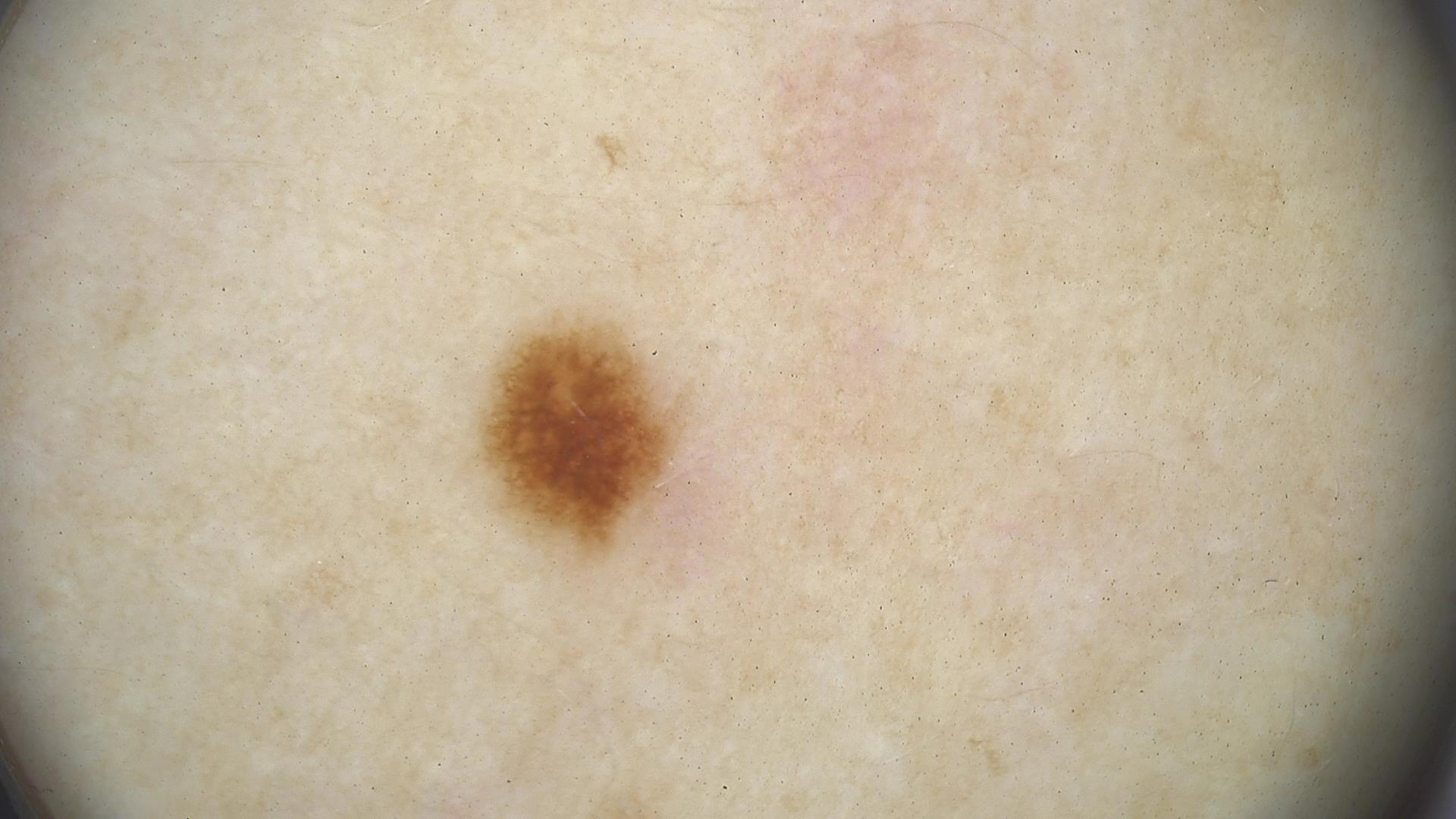A dermoscopic image of a skin lesion.
Diagnosed as a banal lesion — a junctional nevus.